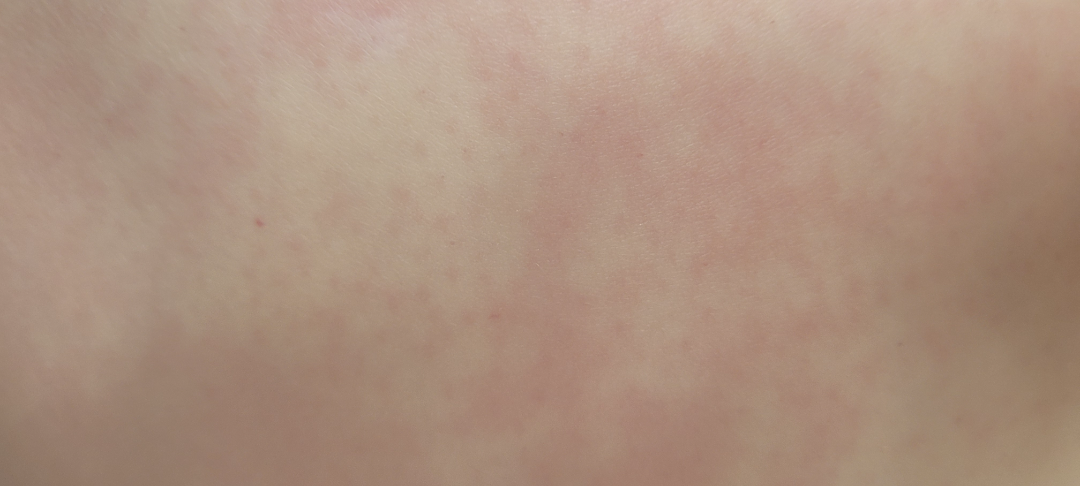The case was difficult to assess from the available photograph.
A close-up photograph.
The affected area is the arm and front of the torso.
The patient indicates enlargement.
Associated systemic symptoms include fatigue, fever and chills.